A dermoscopic image of a skin lesion.
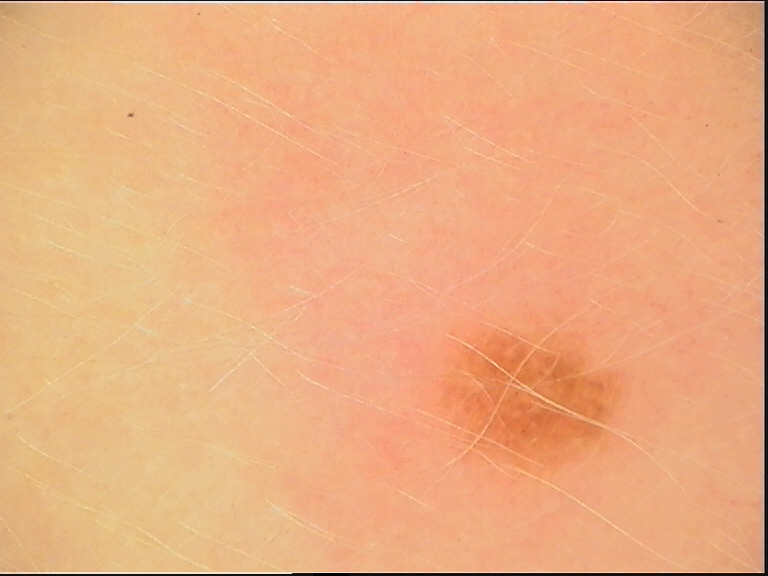Diagnosed as a dysplastic junctional nevus.